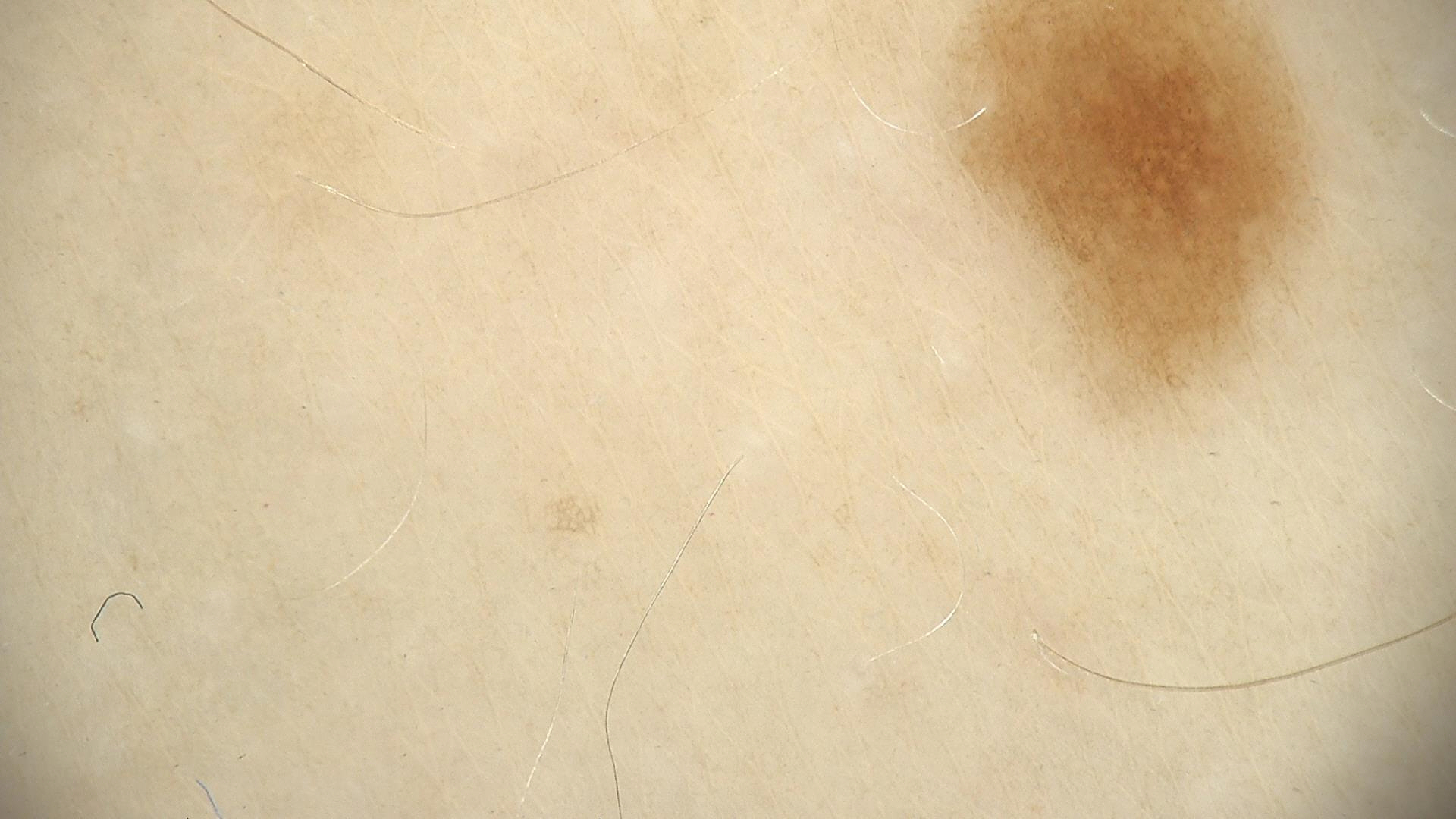Q: What is the diagnosis?
A: dysplastic junctional nevus (expert consensus)